Dermoscopy of a skin lesion.
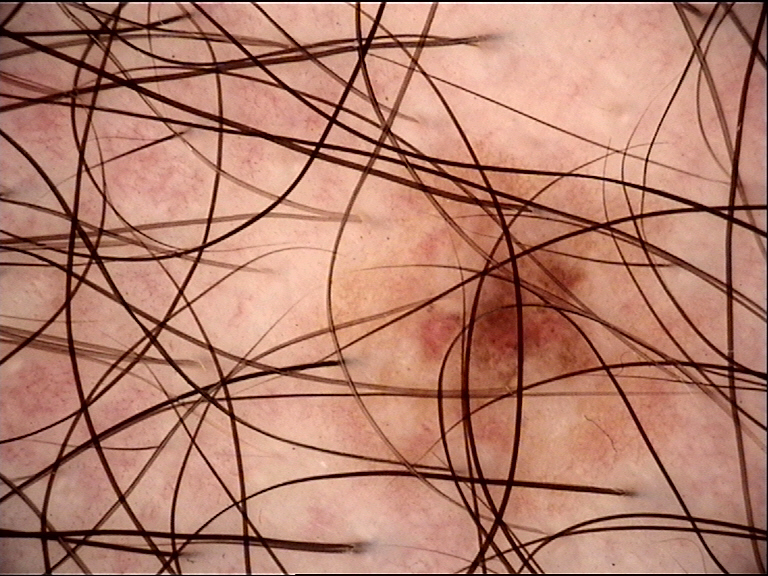Conclusion: The diagnostic label was a dysplastic junctional nevus.